The chart records prior skin cancer (patient or family) and no prior malignancy (patient or family) · the patient is skin type II · a female subject 73 years of age.
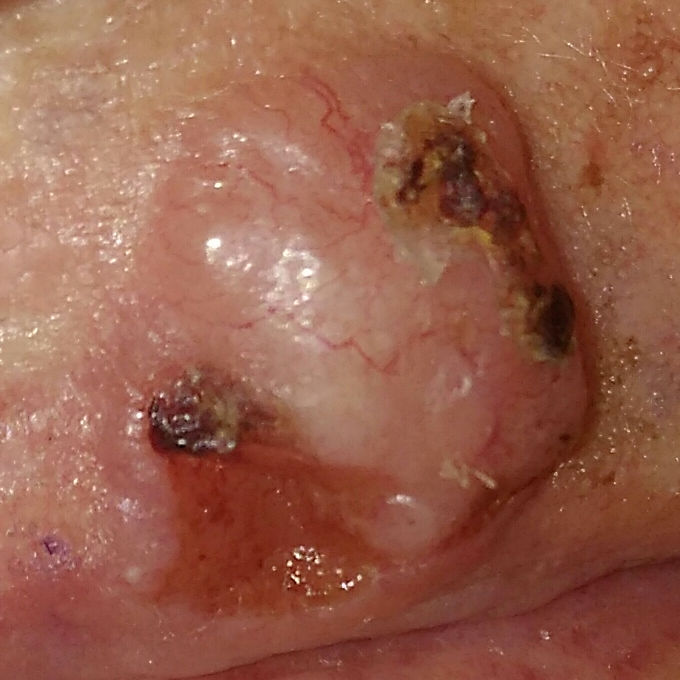Case:
- anatomic site · a lip
- diameter · approx. 18 × 16 mm
- symptoms · itching, pain, elevation, bleeding
- pathology · basal cell carcinoma (biopsy-proven)